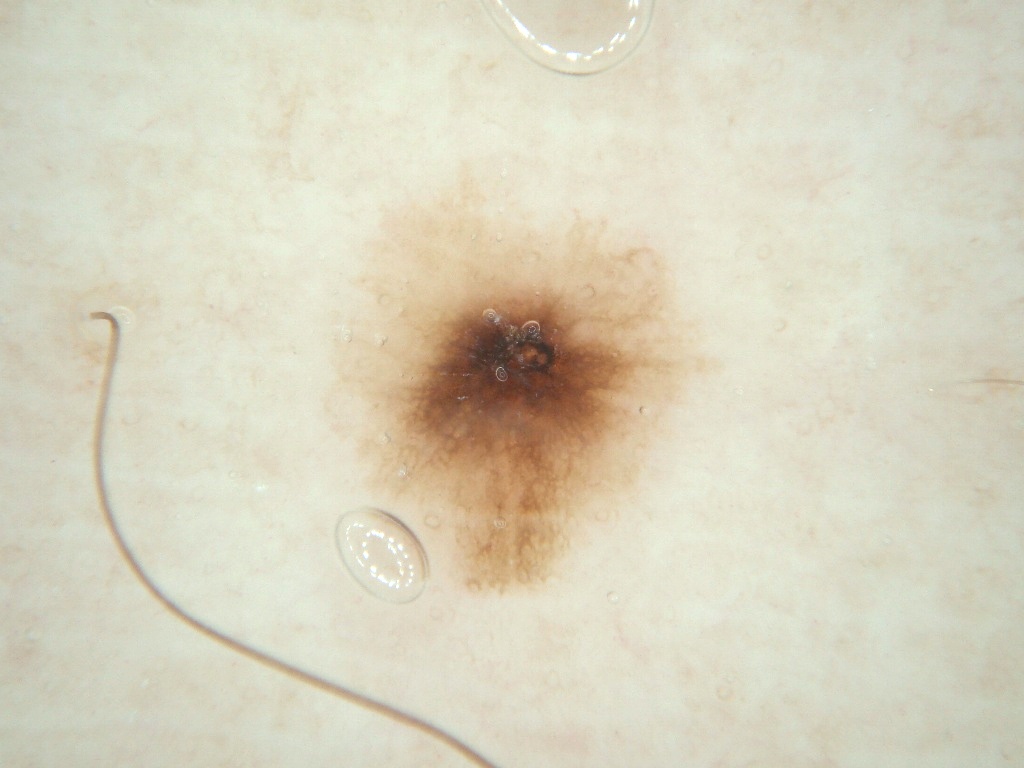patient:
  sex: female
  age_approx: 60
image:
  modality: dermoscopy
lesion_extent:
  approx_field_fraction_pct: 12
dermoscopic_features:
  present:
    - pigment network
  absent:
    - milia-like cysts
    - streaks
    - negative network
    - globules
lesion_location:
  bbox_xyxy:
    - 339
    - 209
    - 707
    - 595
diagnosis:
  name: melanocytic nevus
  malignancy: benign
  lineage: melanocytic
  provenance: clinical